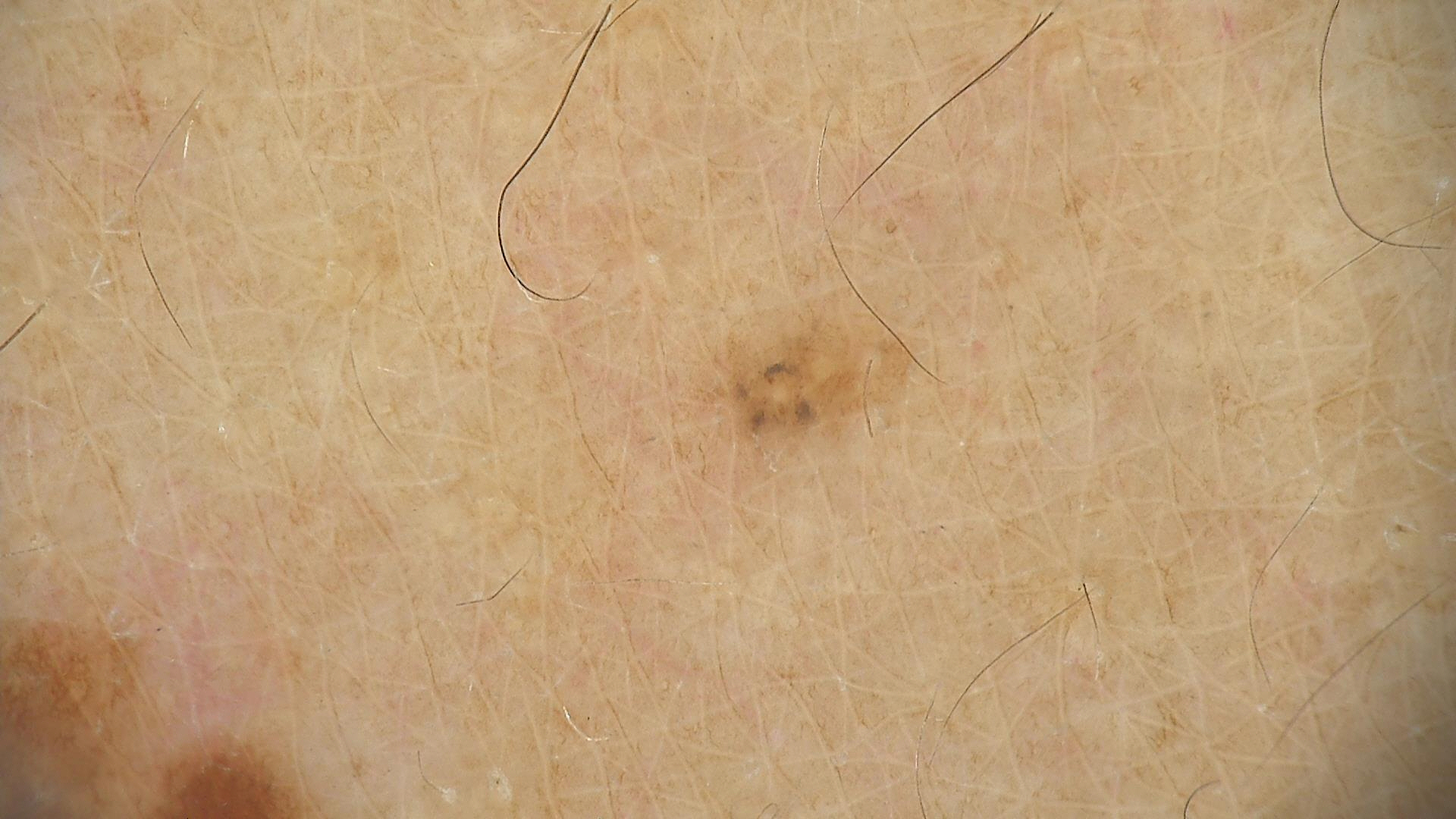| field | value |
|---|---|
| class | dysplastic junctional nevus (expert consensus) |